A dermoscopic image of a skin lesion. A female subject age 84. The patient says their skin tans without first burning. The patient describes having few moles overall. The patient reports a personal history of cancer:
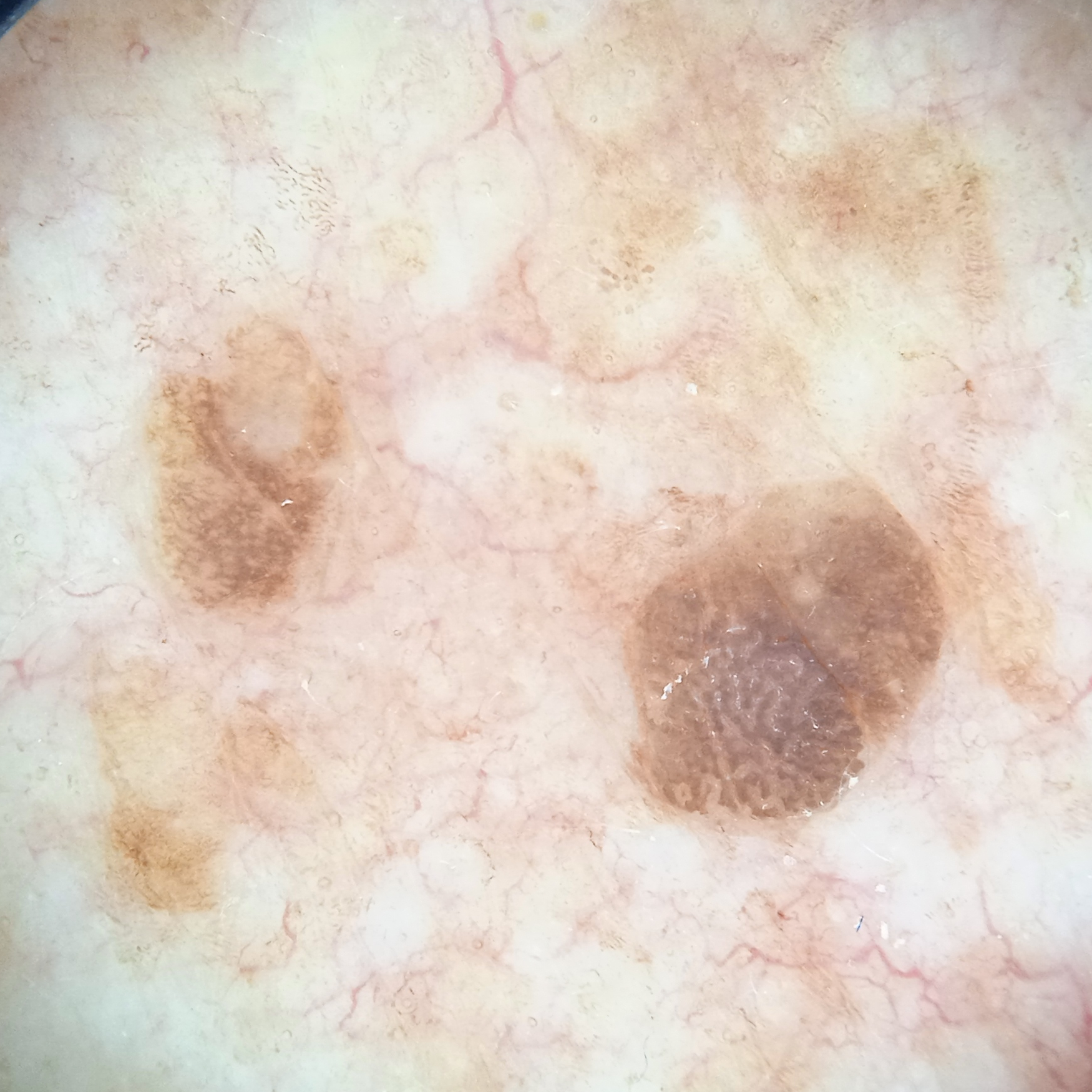body site: the torso | size: 4.6 mm | assessment: seborrheic keratosis (dermatologist consensus).